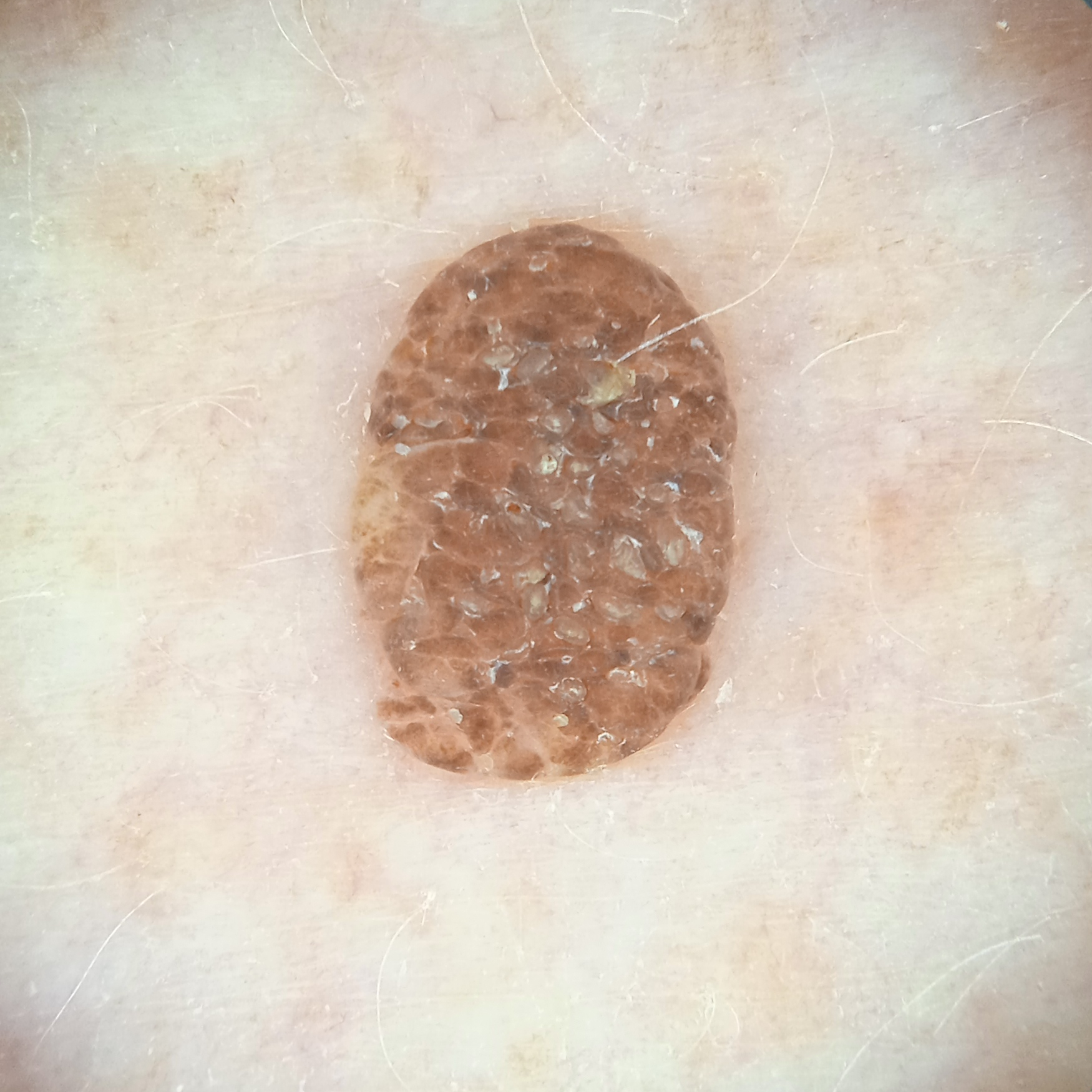<lesion>
  <mole_burden>numerous melanocytic nevi</mole_burden>
  <referral>research study (no referral diagnosis)</referral>
  <patient>
    <age>78</age>
    <sex>female</sex>
  </patient>
  <sun_reaction>skin tans without first burning</sun_reaction>
  <risk_factors>
    <negative>no sunbed use</negative>
  </risk_factors>
  <image>dermoscopy</image>
  <lesion_location>an arm</lesion_location>
  <lesion_size>
    <diameter_mm>5.6</diameter_mm>
  </lesion_size>
  <diagnosis>
    <name>seborrheic keratosis</name>
    <malignancy>benign</malignancy>
  </diagnosis>
</lesion>